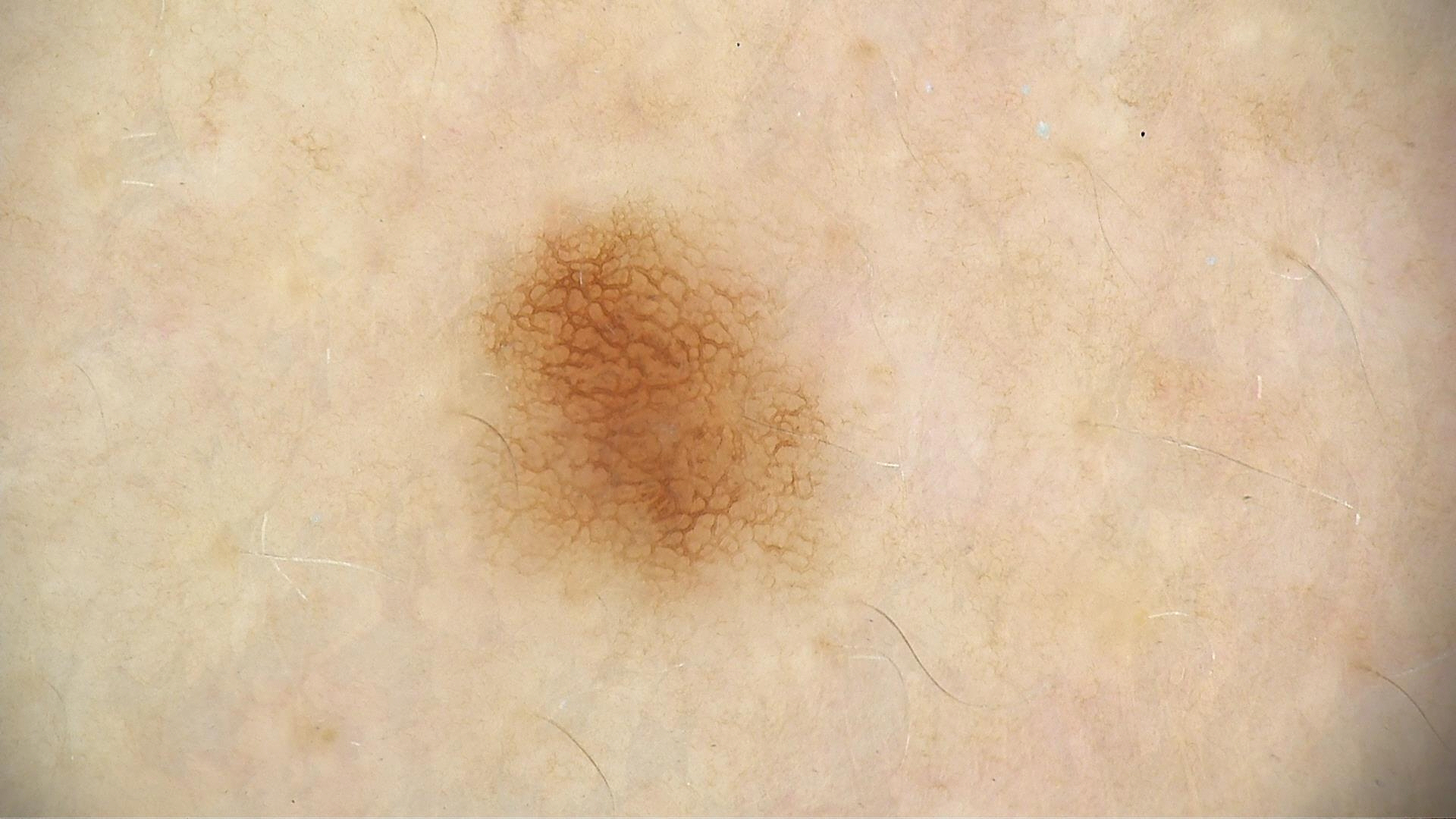• diagnosis: dysplastic junctional nevus (expert consensus)